Per the chart, a previous melanoma · a male subject in their mid-80s or older · a dermoscopy image of a single skin lesion · the patient is skin type II.
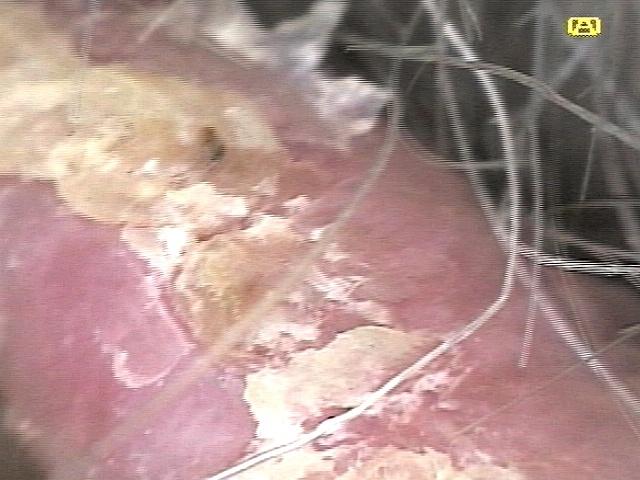Summary:
The lesion is on the head or neck.
Assessment:
The diagnostic impression was a solar or actinic keratosis.